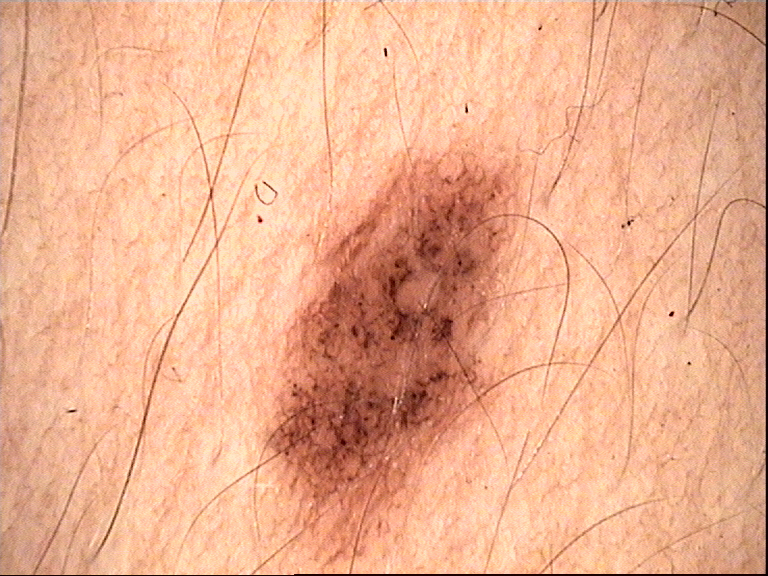The diagnostic label was a benign lesion — a dysplastic junctional nevus.